Dermoscopy of a skin lesion.
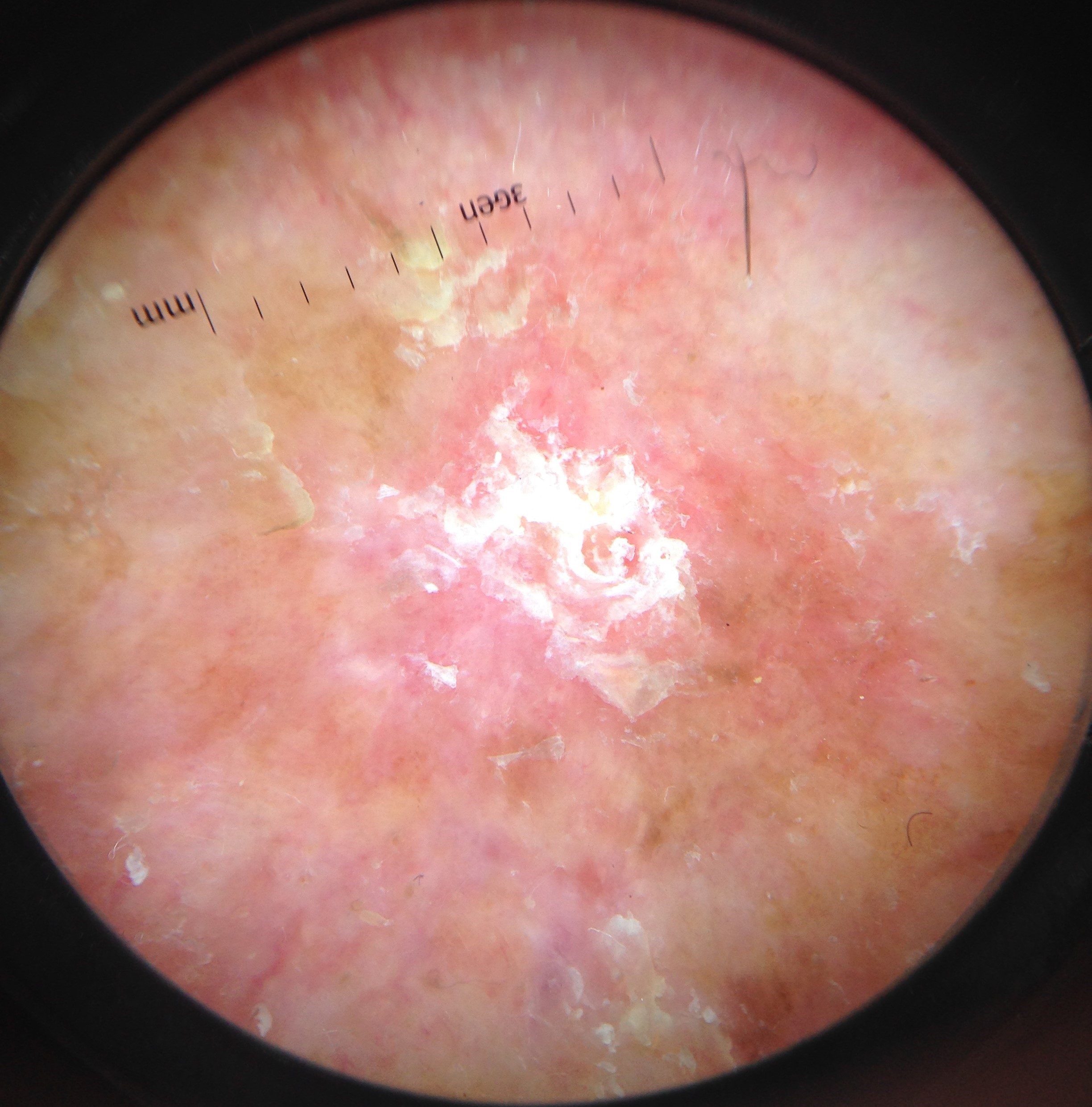The biopsy diagnosis was a keratinocytic, malignant lesion — a squamous cell carcinoma.